The photo was captured at a distance. Located on the leg. The subject is 40–49, male: 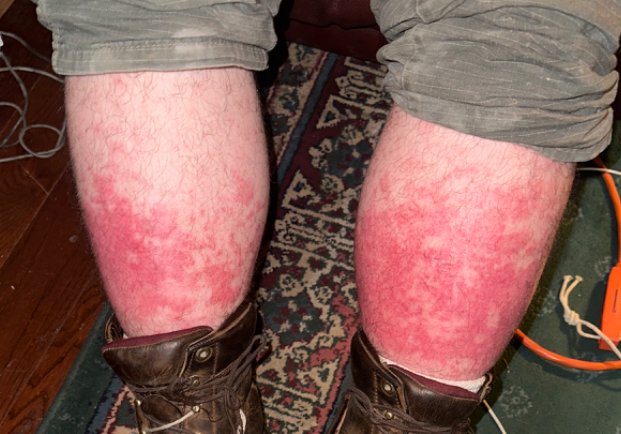assessment: indeterminate from the photograph | lesion texture: raised or bumpy | systemic symptoms: fatigue | symptom duration: less than one week | patient-reported symptoms: pain, bothersome appearance, darkening and enlargement.